The leg is involved · female patient, age 60–69 · a close-up photograph — 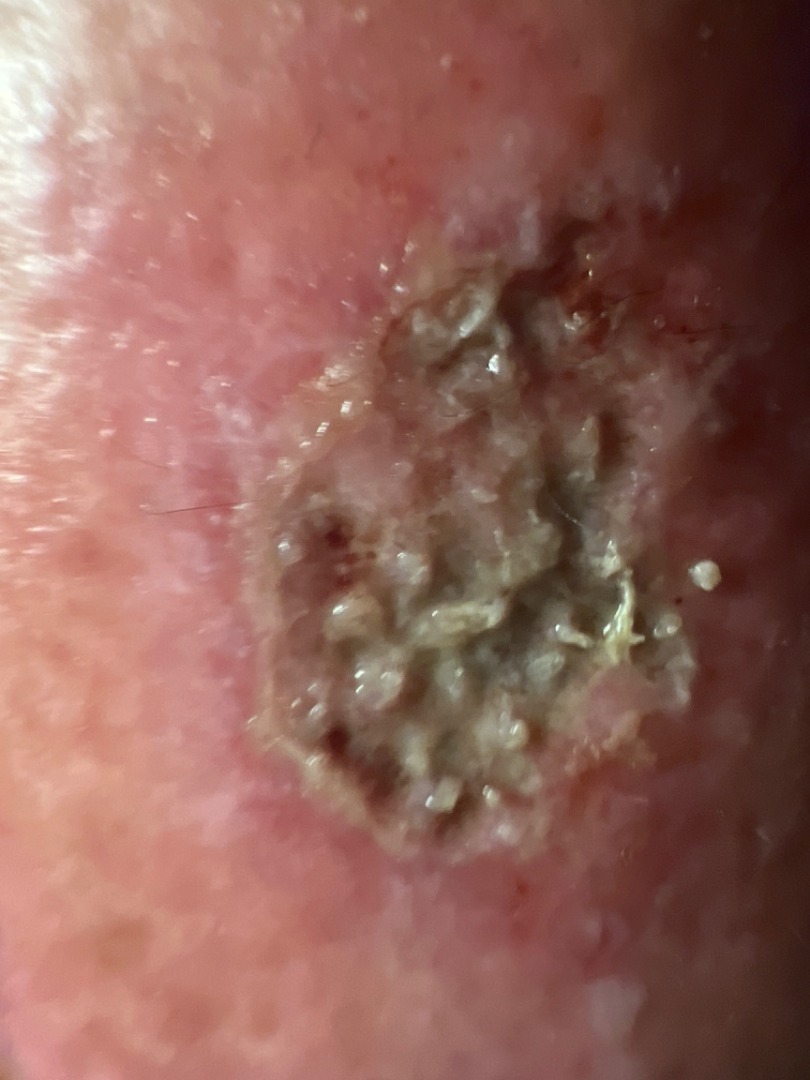The reviewer was unable to grade this case for skin condition.